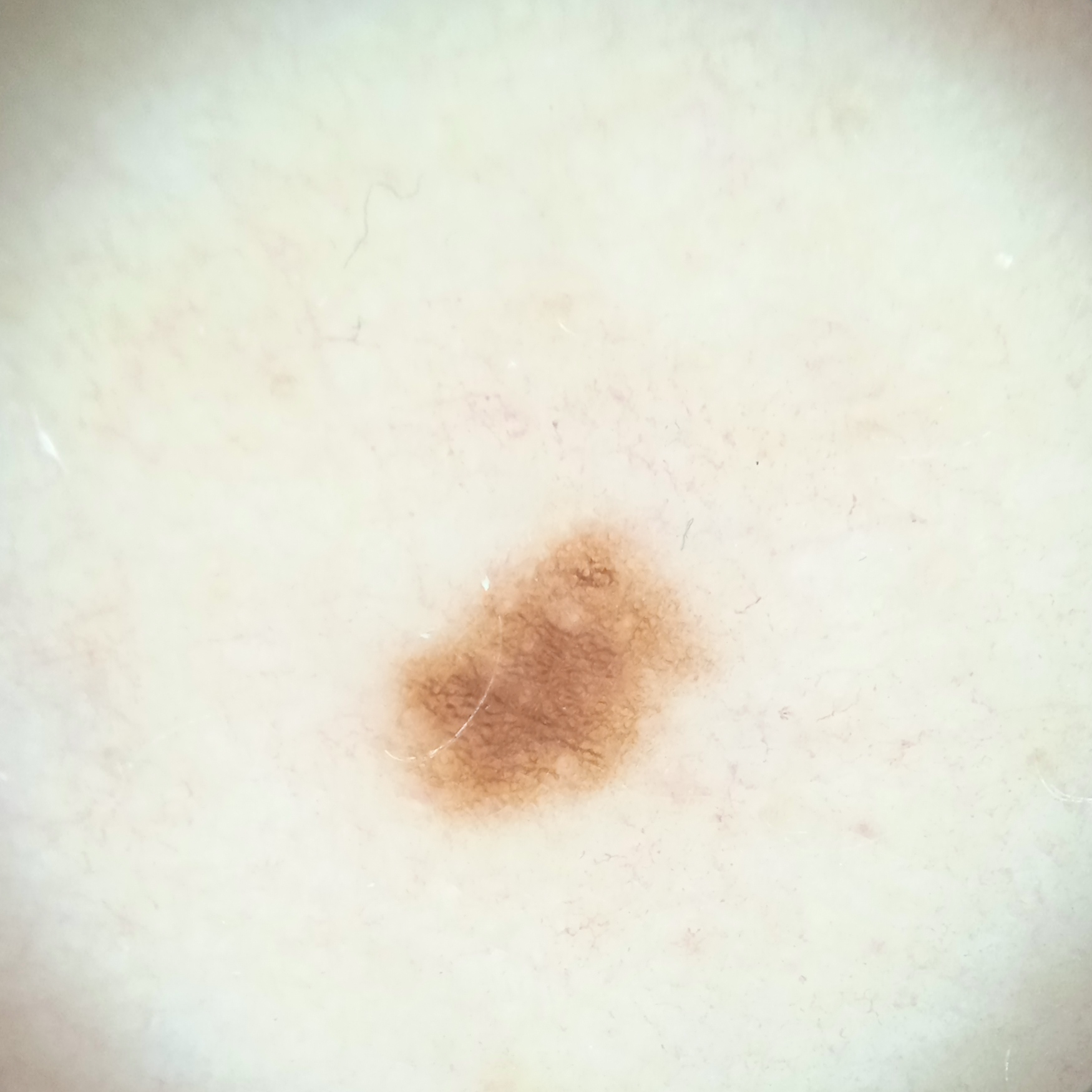A female patient aged 48.
The patient says their skin reddens painfully with sun exposure.
A dermoscopic image of a skin lesion.
The patient reports a history of sunbed use, a family history of skin cancer, and no prior organ transplant.
Few moles overall by the patient's own estimate.
Collected as part of a research study, without a referral diagnosis.
Located on the torso.
Measuring roughly 4.3 mm.
On independent review by four dermatologists, the agreed diagnosis was a melanocytic nevus; the reviewers were highly confident; reviewers noted it may also be a solar lentigo.